Reported lesion symptoms include bothersome appearance and itching · present for less than one week · the lesion involves the arm · the patient considered this a rash · the lesion is described as raised or bumpy · this image was taken at a distance — 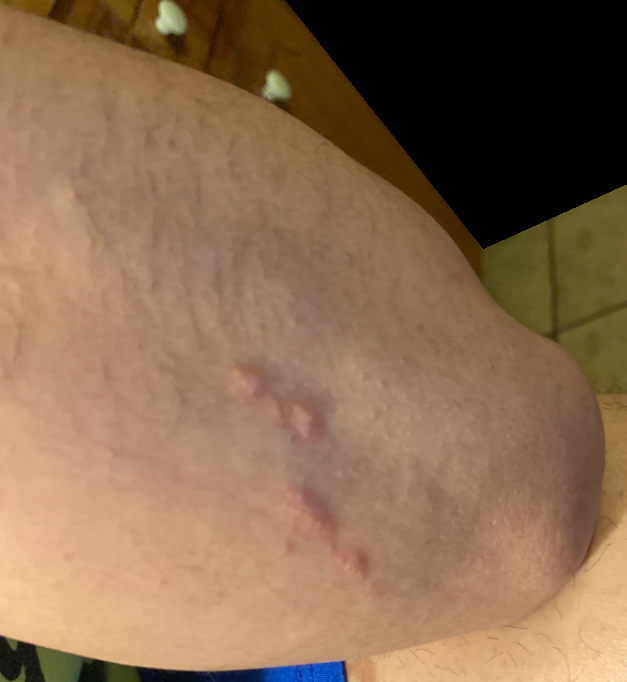assessment = indeterminate.